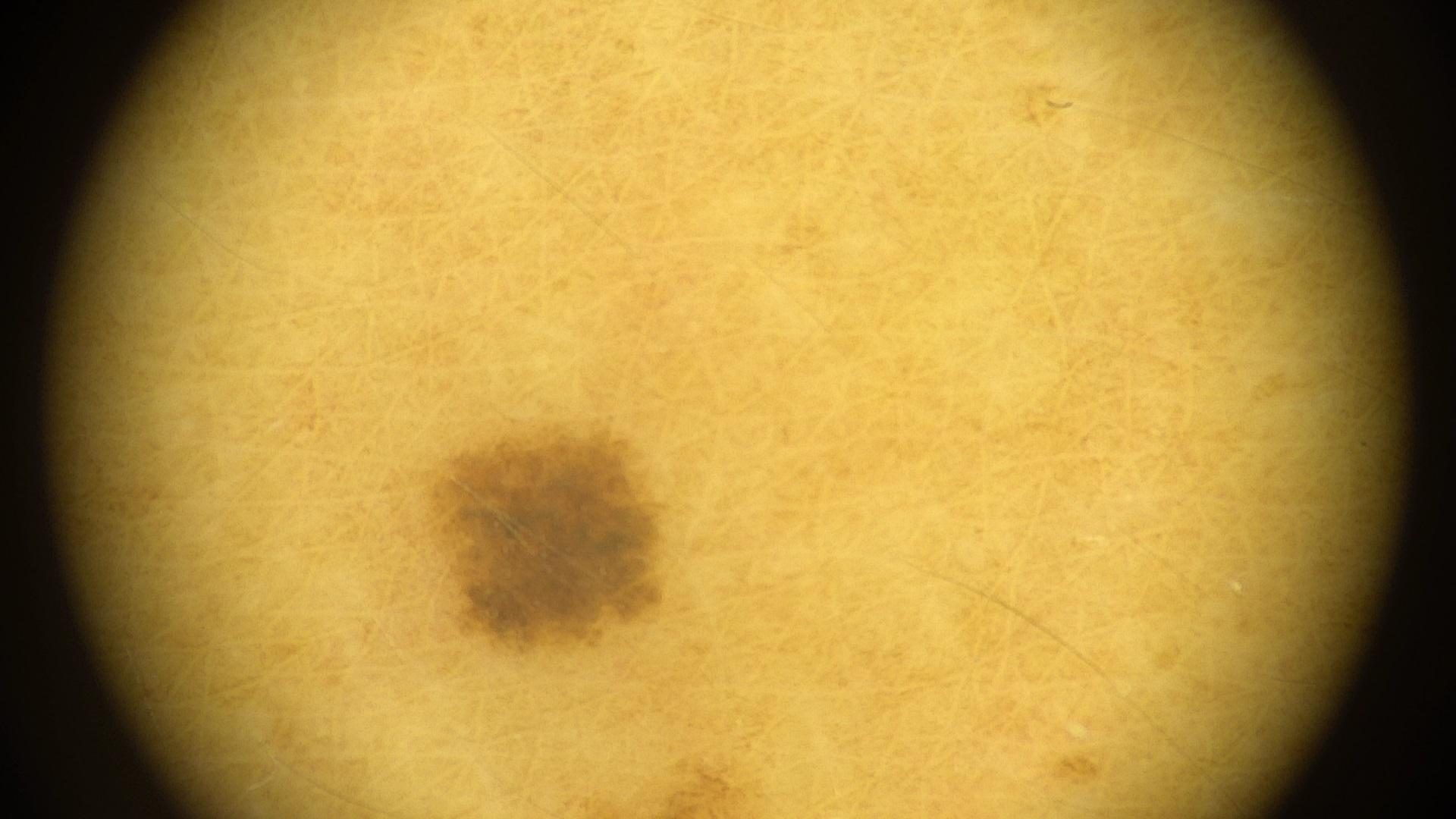| field | value |
|---|---|
| assessment | Nevus |